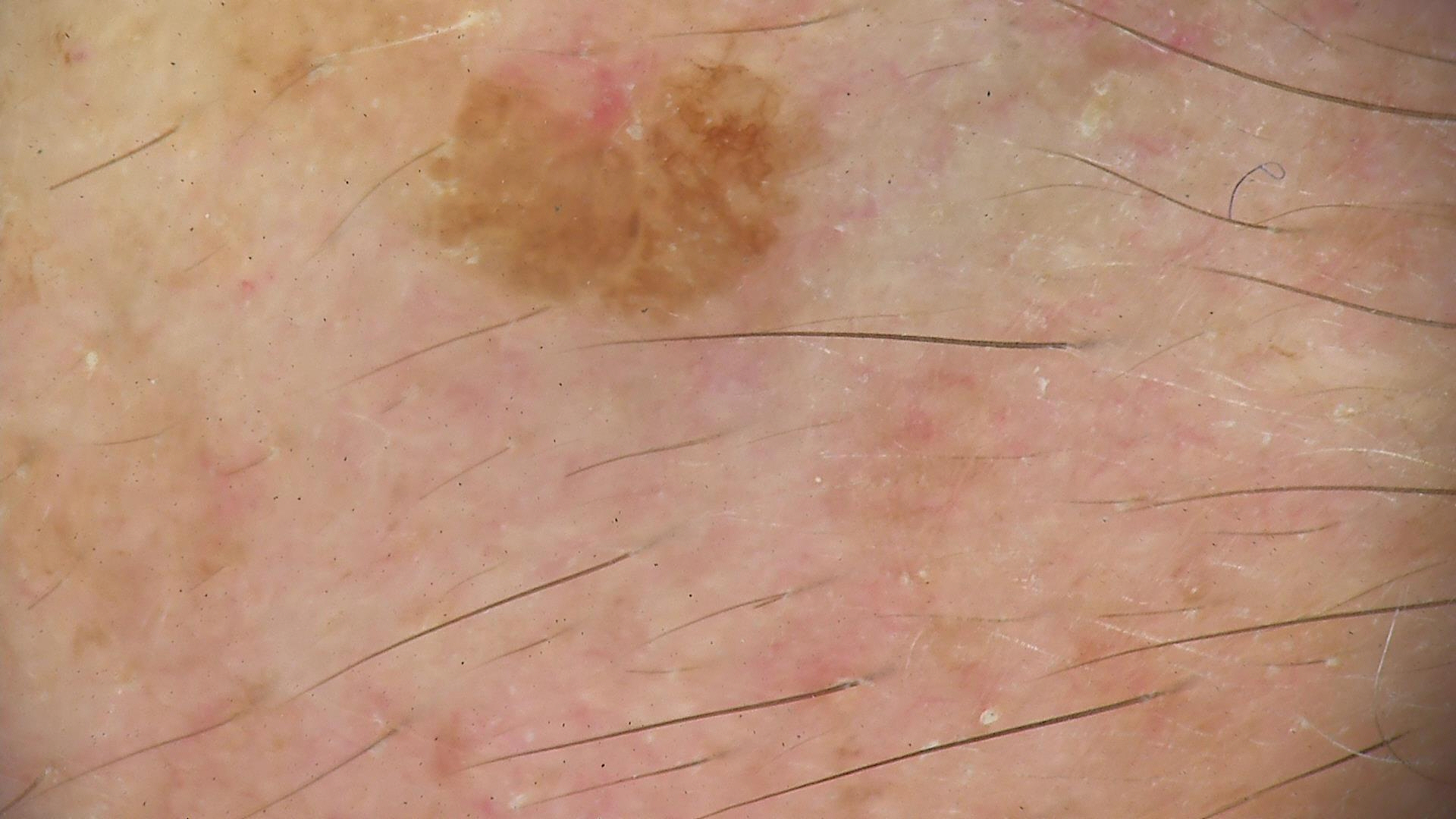Q: What is the diagnosis?
A: seborrheic keratosis (expert consensus)